The condition has been present for about one day · the patient indicates the lesion is raised or bumpy · the contributor is a female aged 18–29 · skin tone: Fitzpatrick II · the lesion involves the leg · the photograph is a close-up of the affected area · the patient indicates pain, enlargement and bothersome appearance · the patient described the issue as a rash · no relevant systemic symptoms:
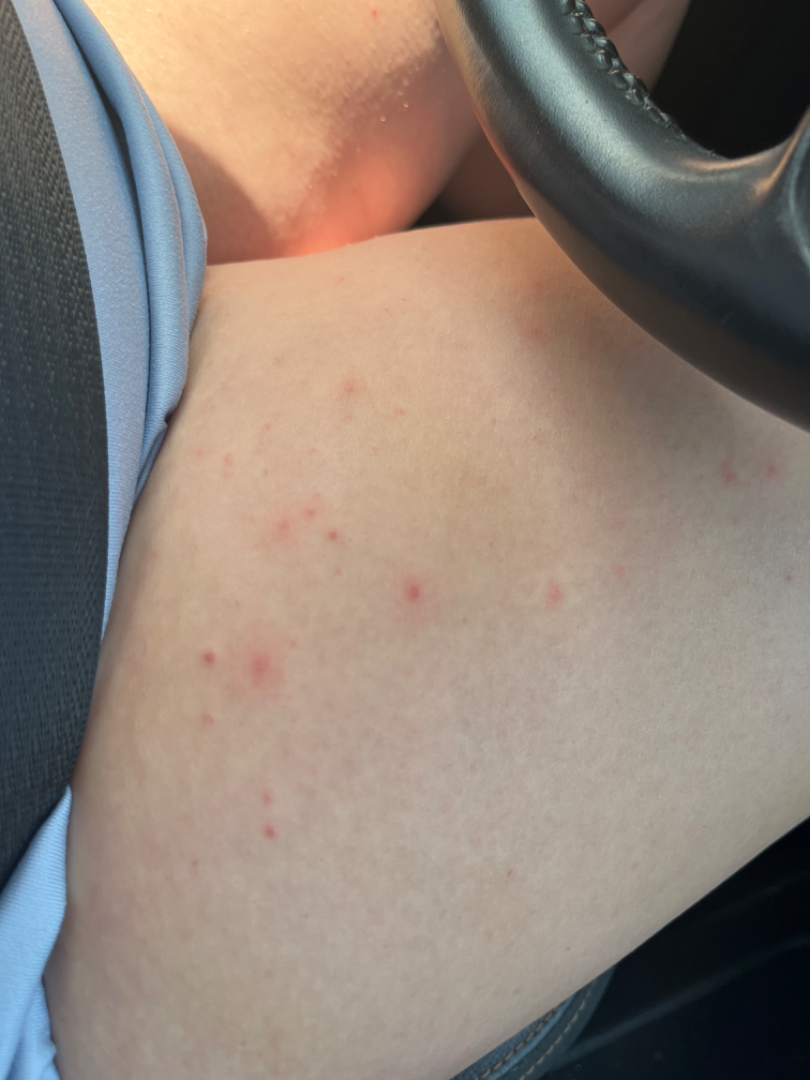On dermatologist assessment of the image, most consistent with Folliculitis; also consider Keratosis pilaris; with consideration of Irritant Contact Dermatitis.